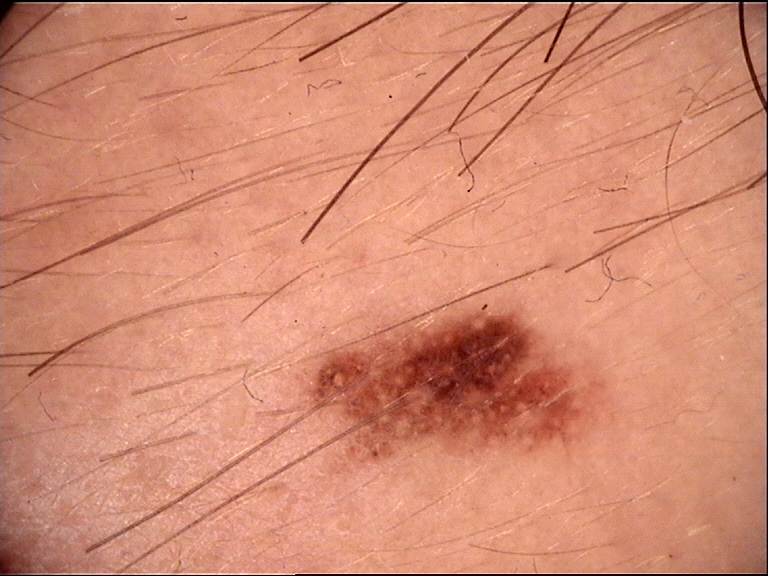image type: dermoscopy
diagnostic label: dysplastic junctional nevus (expert consensus)